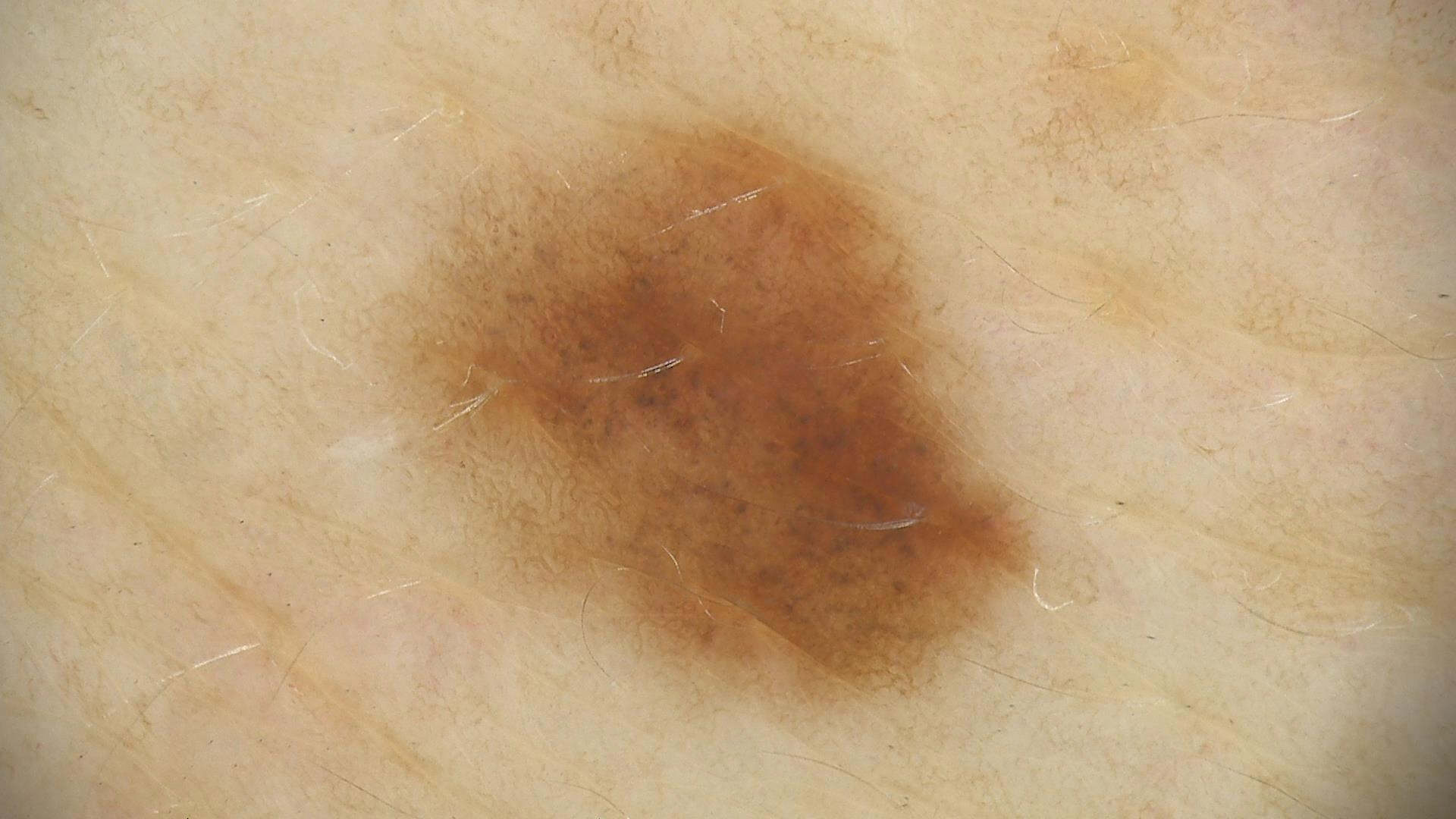Case:
– diagnostic label — dysplastic junctional nevus (expert consensus)